The condition has been present for one to three months. An image taken at a distance. Self-reported FST IV. The patient described the issue as a rash. The leg is involved. The lesion is described as flat. Reported lesion symptoms include enlargement and itching. The contributor is male:
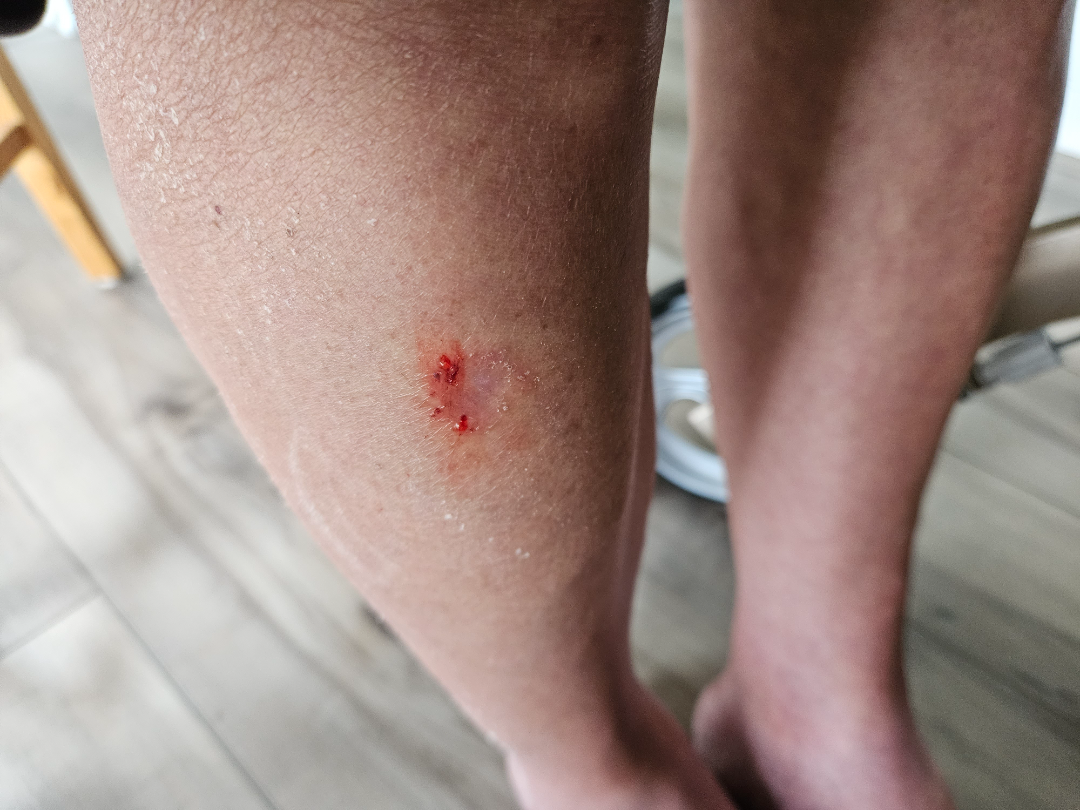<dermatology_case>
  <assessment>ungradable on photographic review</assessment>
</dermatology_case>